A male subject, aged around 15; a dermoscopic close-up of a skin lesion: 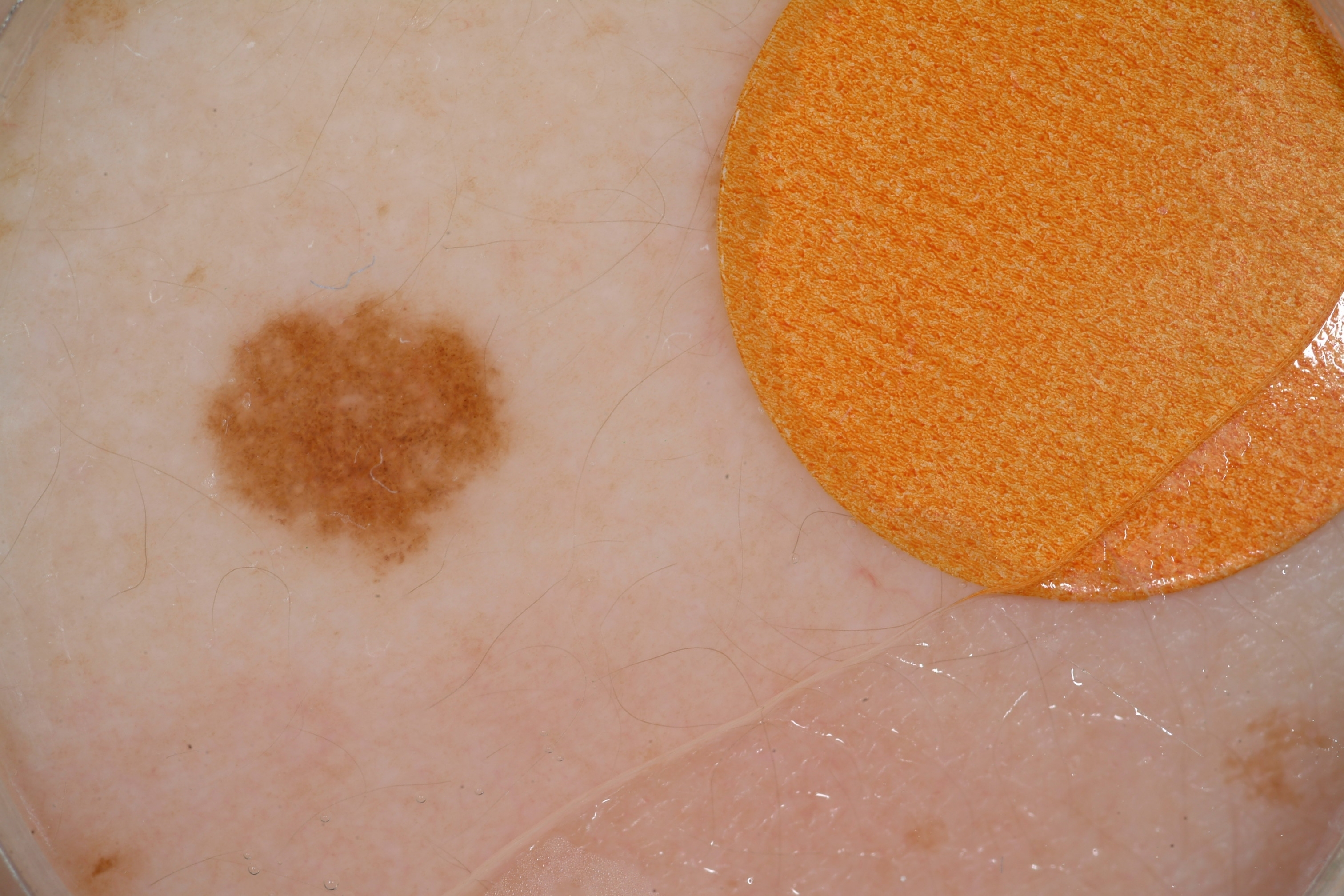Q: Which assessed dermoscopic features were absent?
A: negative network, pigment network, streaks, and milia-like cysts
Q: What is the lesion's bounding box?
A: box(189, 277, 522, 601)
Q: Lesion extent?
A: small
Q: What is this lesion?
A: a melanocytic nevus